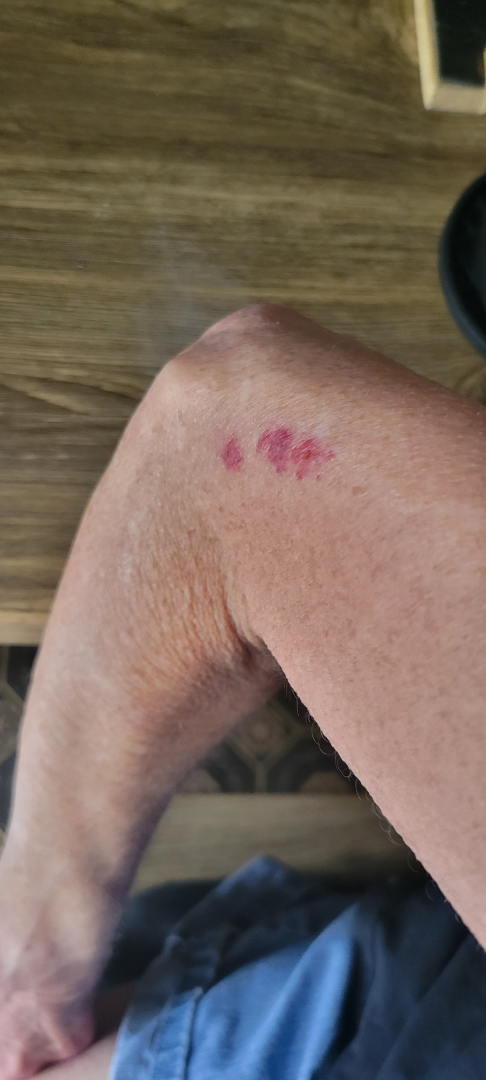On remote dermatologist review: Abrasion, scrape, or scab (possible); Allergic Contact Dermatitis (possible).